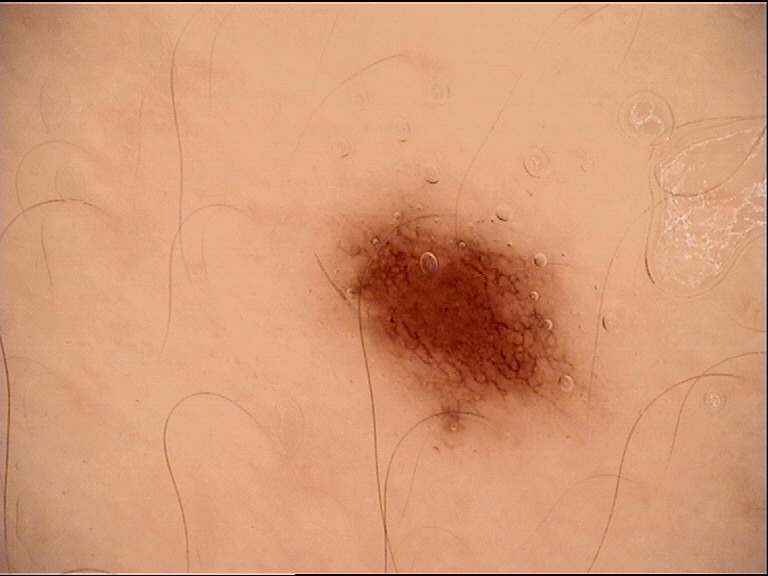diagnostic label: dysplastic junctional nevus (expert consensus).